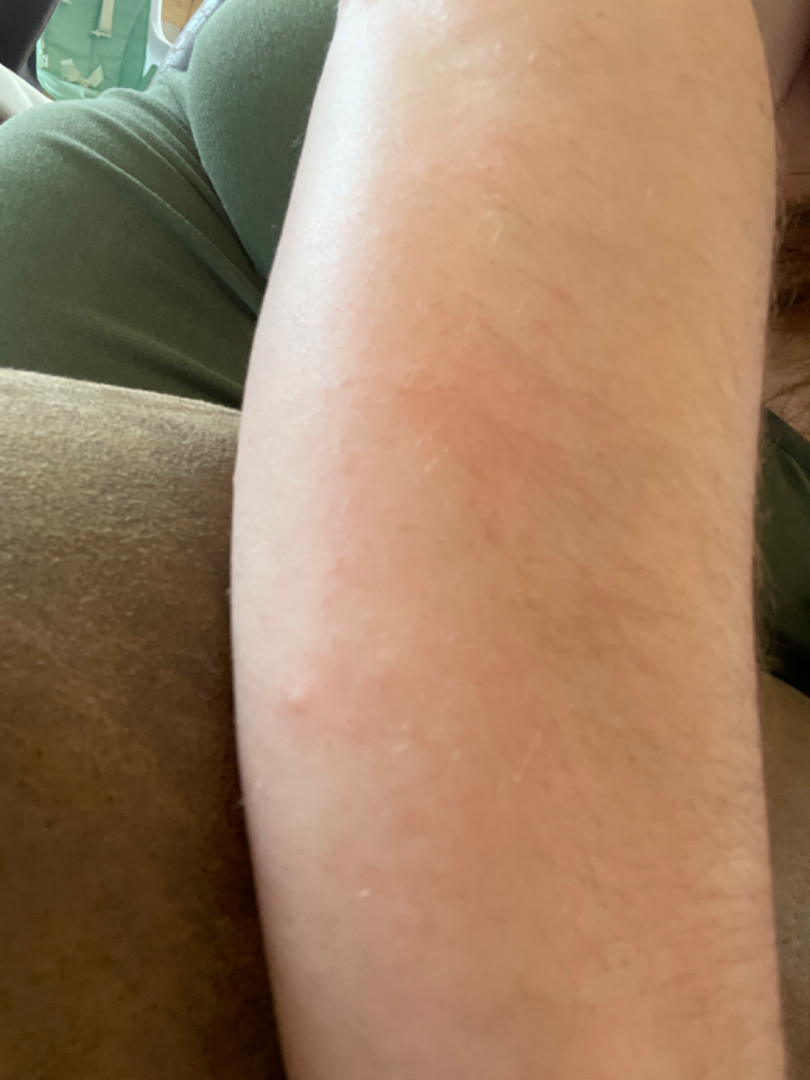On teledermatology review: most consistent with Insect Bite; possibly Allergic Contact Dermatitis; less likely is Scabies.